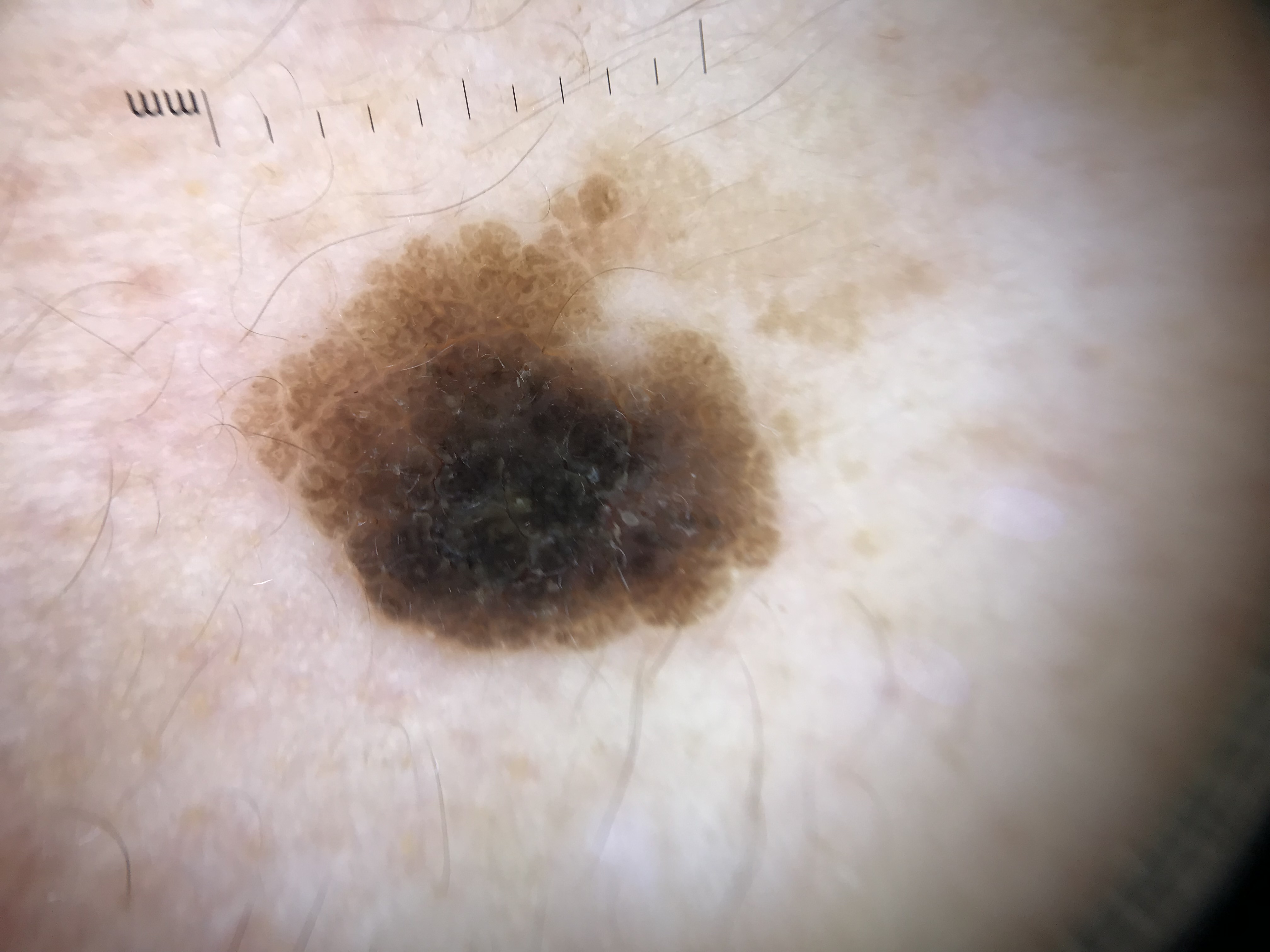The architecture is that of a keratinocytic lesion.
Classified as a seborrheic keratosis.